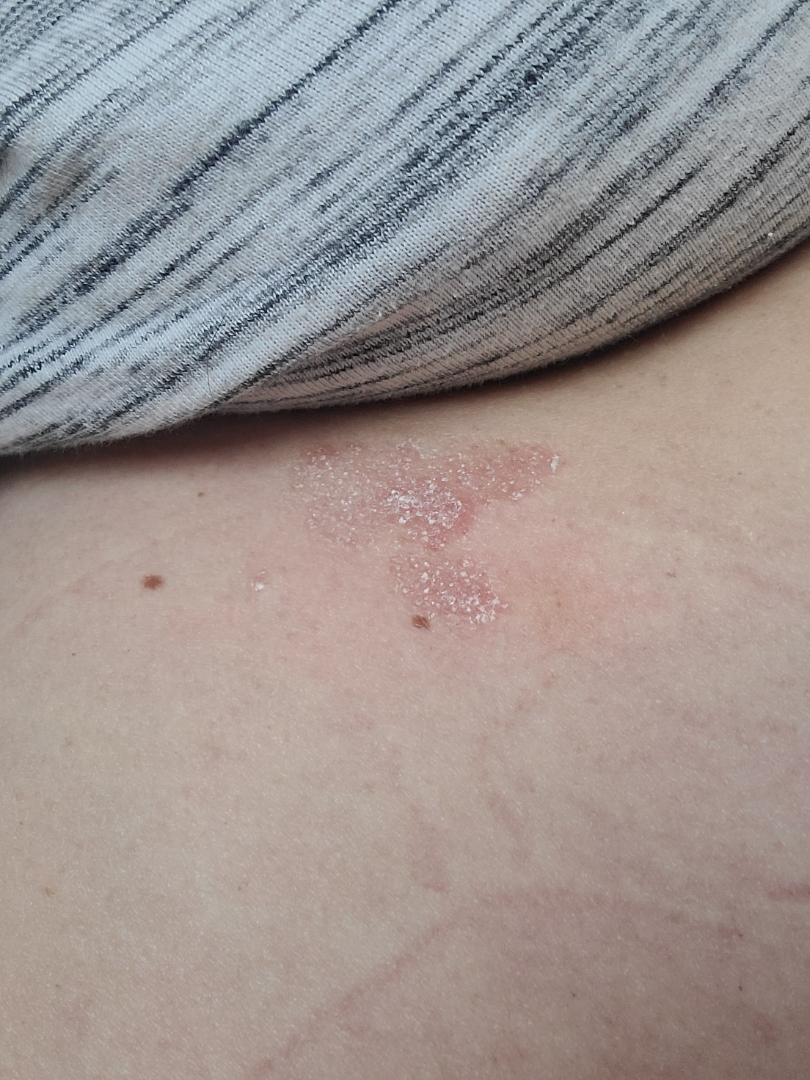  skin_tone:
    fitzpatrick: II
    monk_skin_tone:
      - 2
      - 3
  duration: one to four weeks
  shot_type: at an angle
  patient_category: a rash
  systemic_symptoms: none reported
  symptoms: itching
  differential:
    leading:
      - Psoriasis
    considered:
      - Eczema